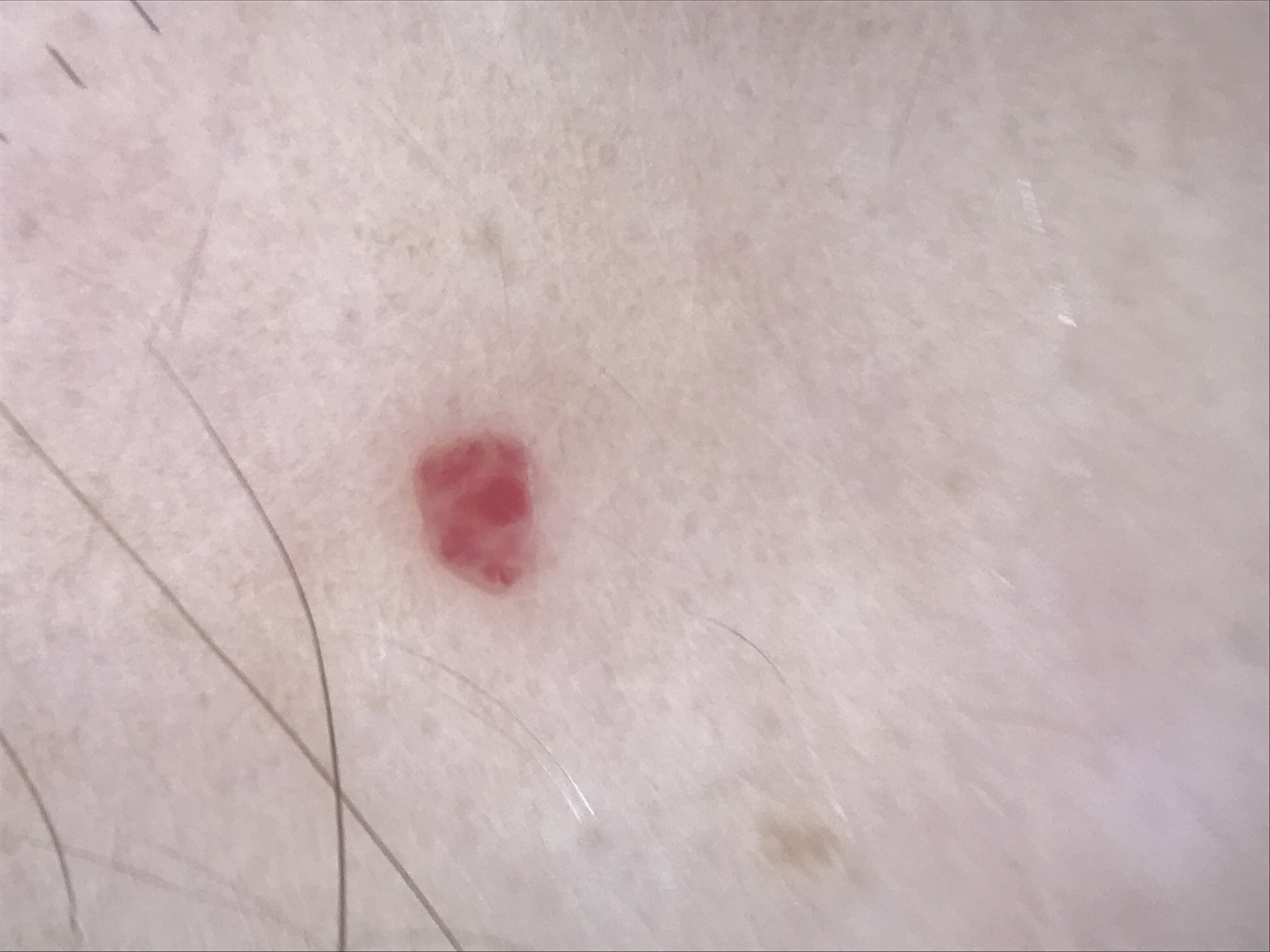Summary:
A dermoscopic photograph of a skin lesion. This is a vascular lesion.
Conclusion:
The diagnostic label was a benign lesion — a hemangioma.